A dermoscopic image of a skin lesion.
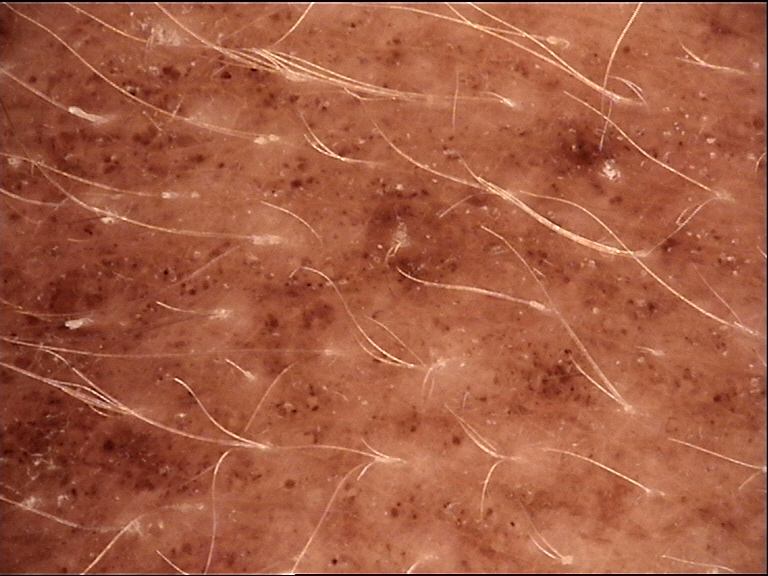Classified as a congenital junctional nevus.